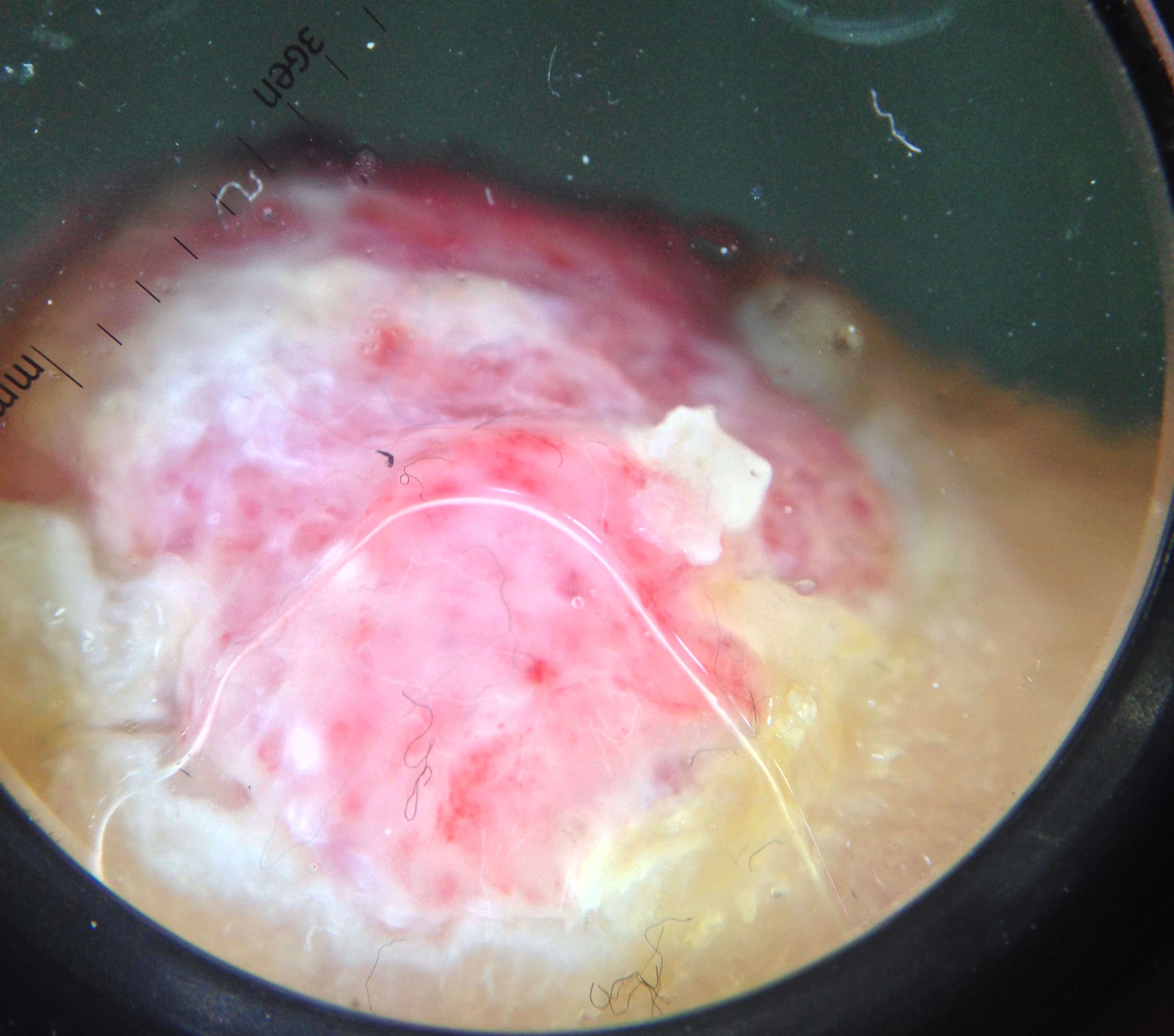image=dermoscopy; label=acral nodular melanoma (biopsy-proven).